The photograph was taken at a distance; the contributor is a female aged 60–69; the leg and top or side of the foot are involved: 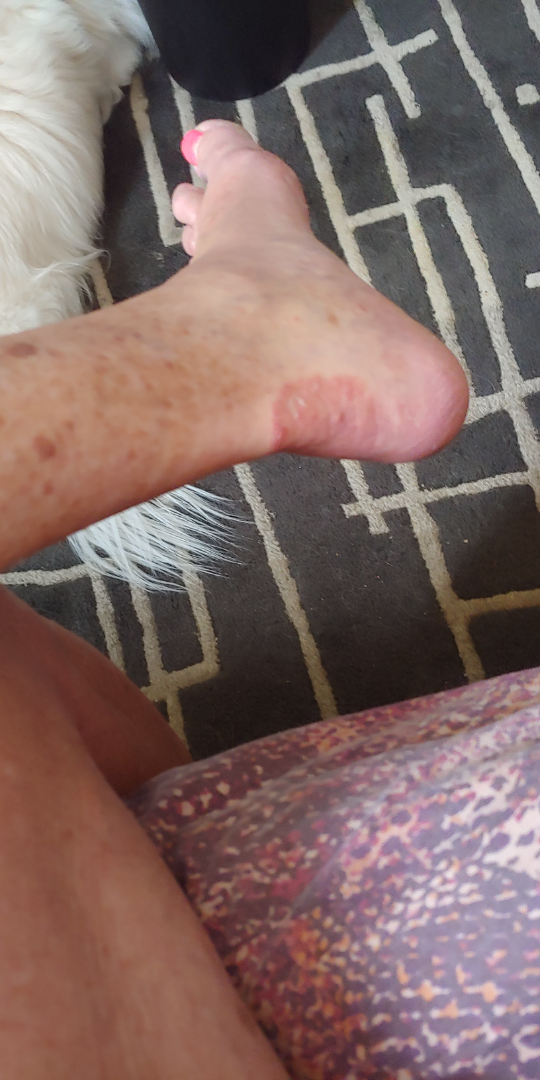assessment = indeterminate from the photograph, described texture = raised or bumpy, patient describes the issue as = a rash, present for = three to twelve months.